Fitzpatrick phototype II; lay graders estimated a Monk Skin Tone of 4 · a close-up photograph · reported lesion symptoms include pain, bothersome appearance, itching and burning · the patient reports the lesion is raised or bumpy · the lesion involves the back of the torso:
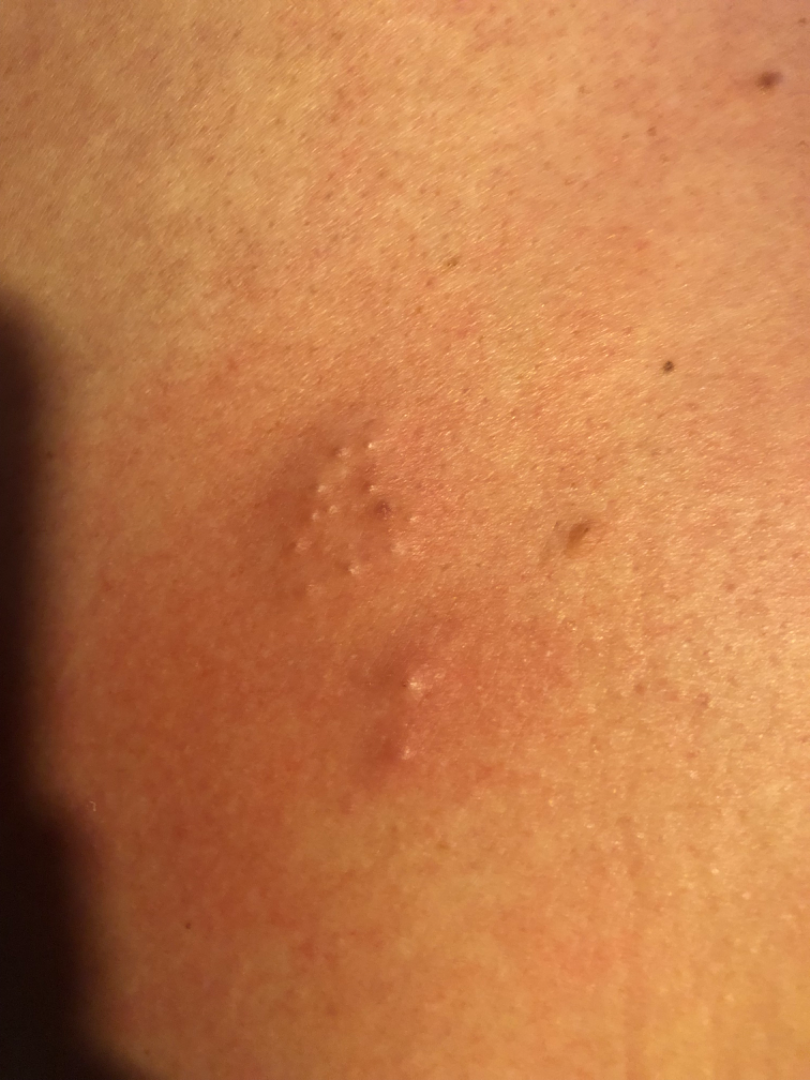Assessment:
Most consistent with Folliculitis; also raised was Herpes Simplex; less probable is Deep fungal infection.